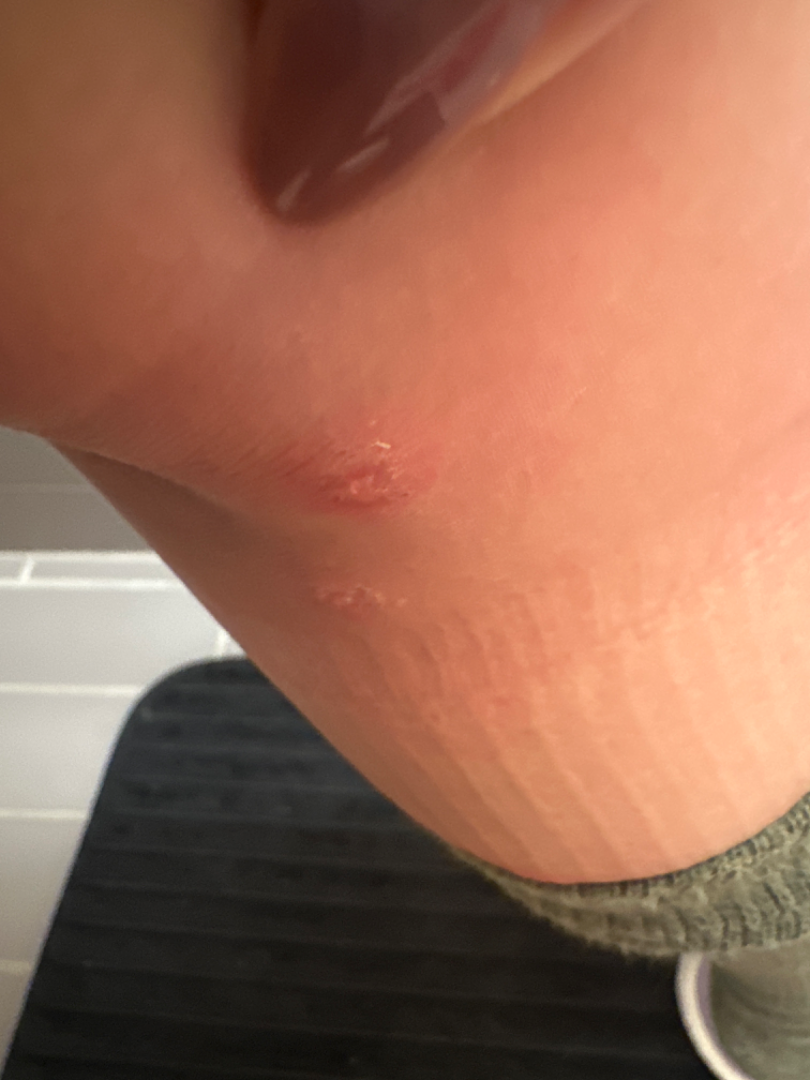Q: What is the differential diagnosis?
A: Psoriasis and Eczema were considered with similar weight